Present for one to four weeks. The patient considered this a rash. The patient notes the lesion is flat. The lesion involves the arm. Reported lesion symptoms include itching. A close-up photograph.
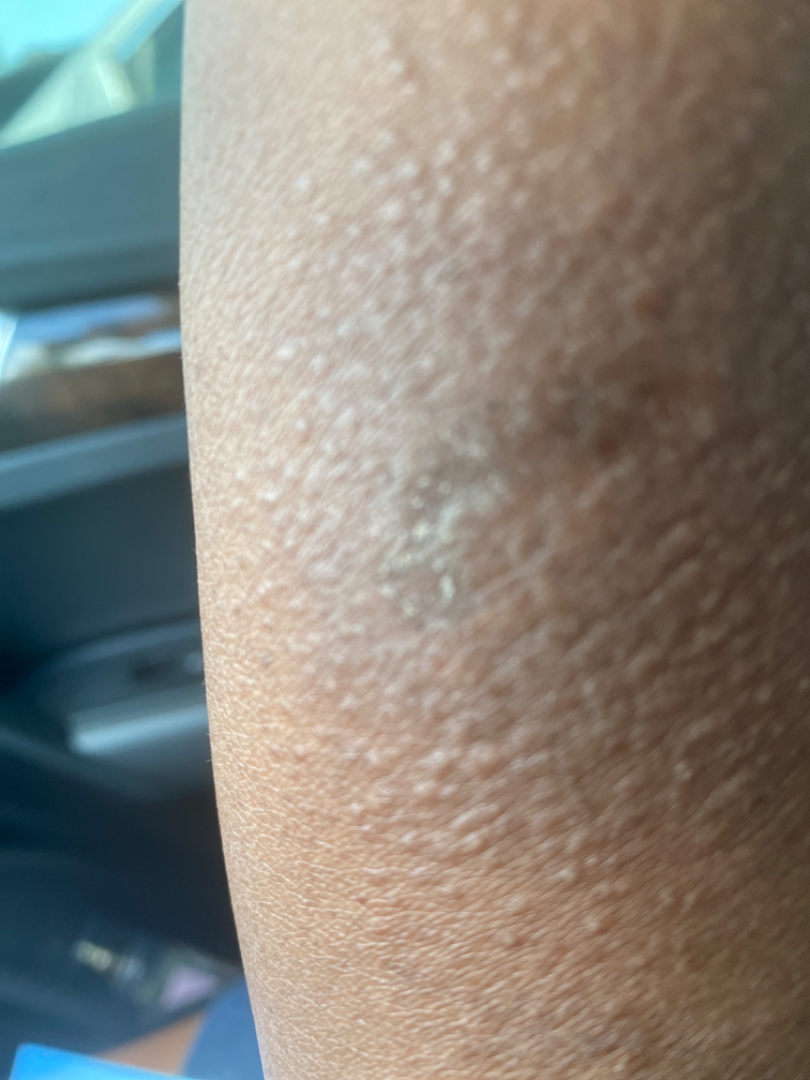| field | value |
|---|---|
| assessment | indeterminate from the photograph |